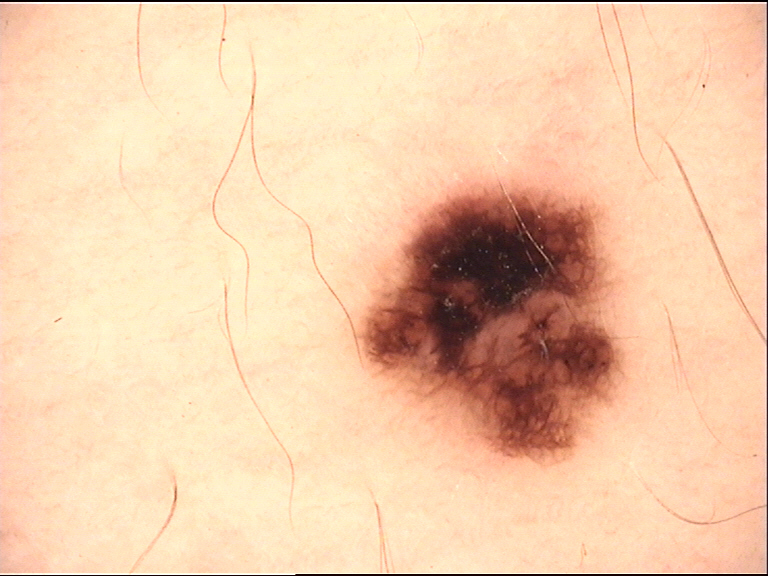Labeled as a dysplastic junctional nevus.